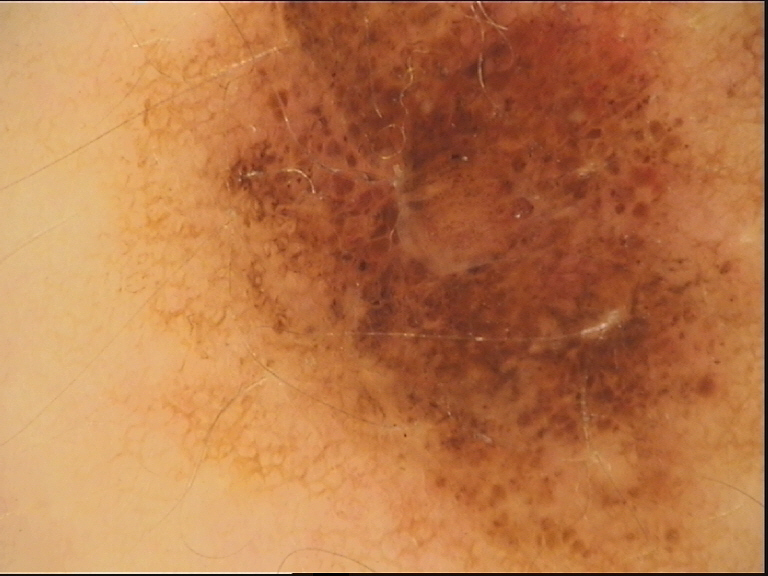class: congenital compound nevus (expert consensus).